A dermoscopic photograph of a skin lesion.
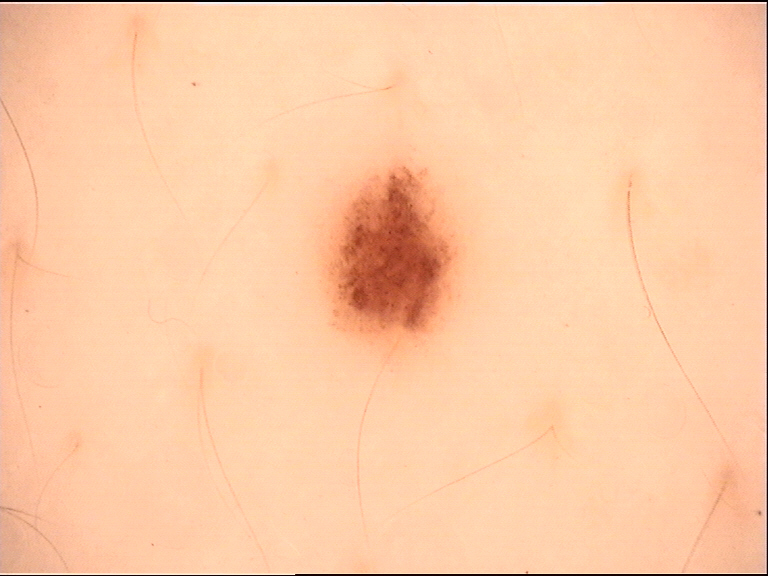Labeled as a benign lesion — a dysplastic junctional nevus.